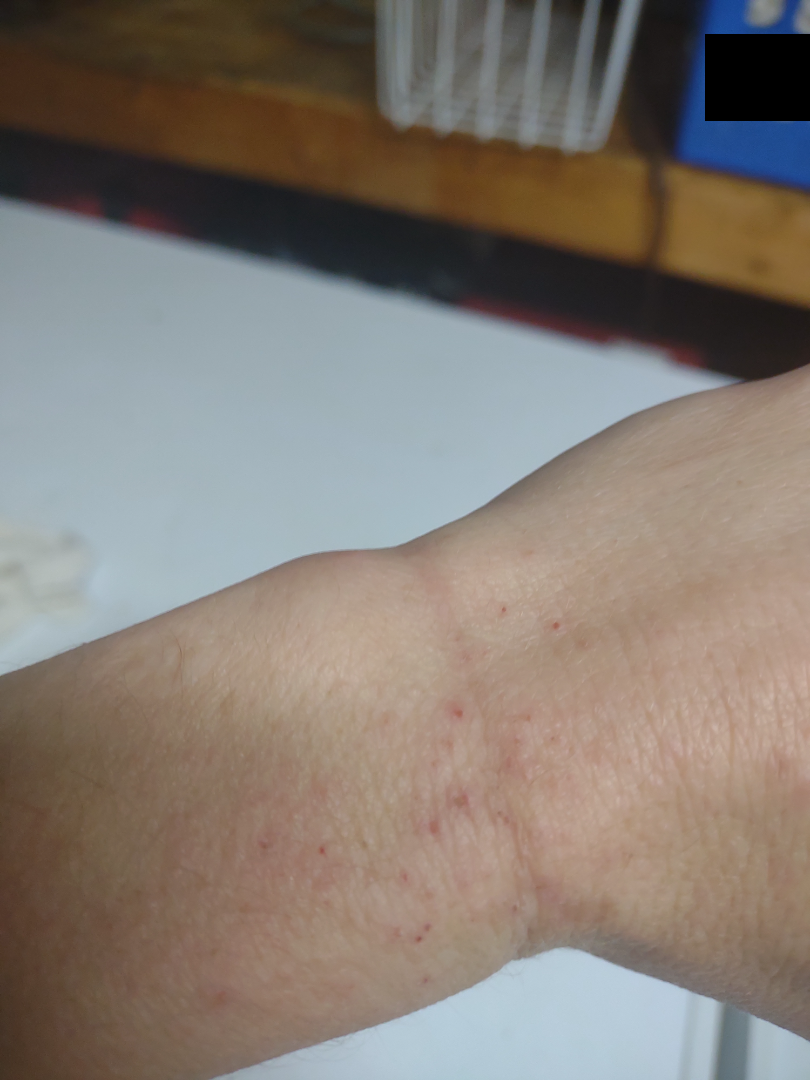Q: Could the case be diagnosed?
A: unable to determine